Reported duration is one to three months, the affected area is the arm, the patient described the issue as skin that appeared healthy to them, a close-up photograph, texture is reported as raised or bumpy:
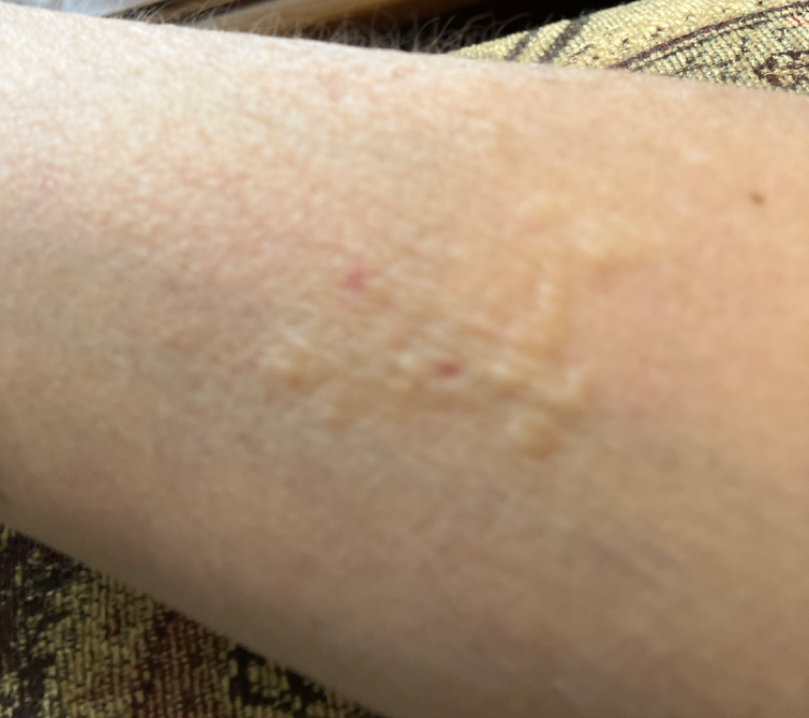The skin condition could not be confidently assessed from this image.